A dermatoscopic image of a skin lesion:
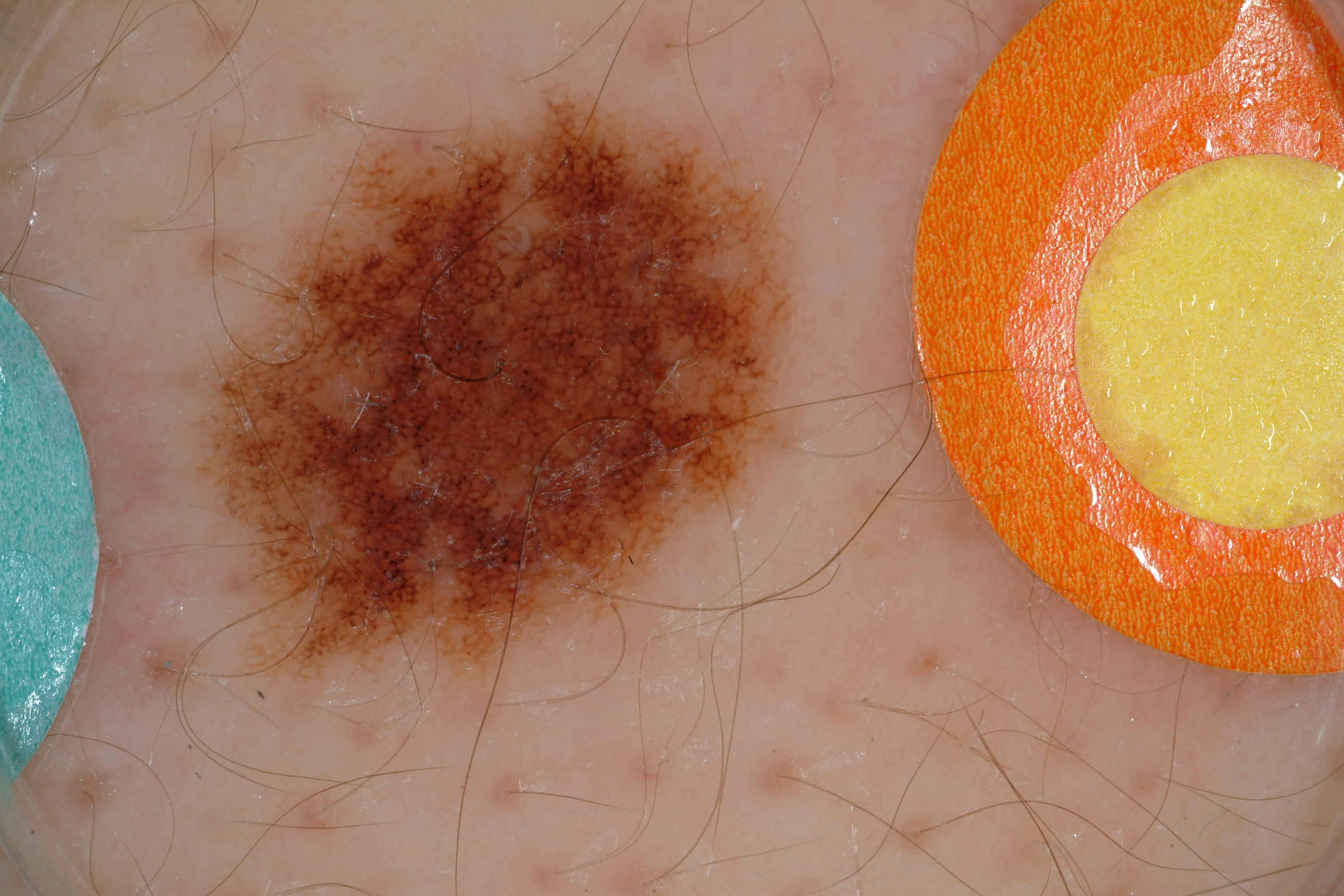A mid-sized lesion within the field. As (left, top, right, bottom), the lesion's extent is [181, 63, 831, 715]. Dermoscopic examination shows globules. The diagnostic assessment was a benign lesion.